The subject is 50–59, female; the patient indicates associated joint pain; the patient indicates the condition has been present for one to four weeks; the head or neck, arm and front of the torso are involved; the photograph is a close-up of the affected area; the patient indicates itching; the lesion is described as flat — 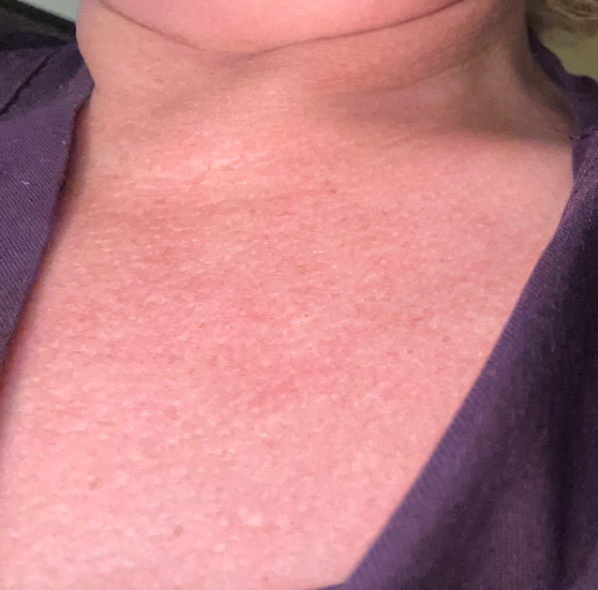  assessment: no discernible pathology